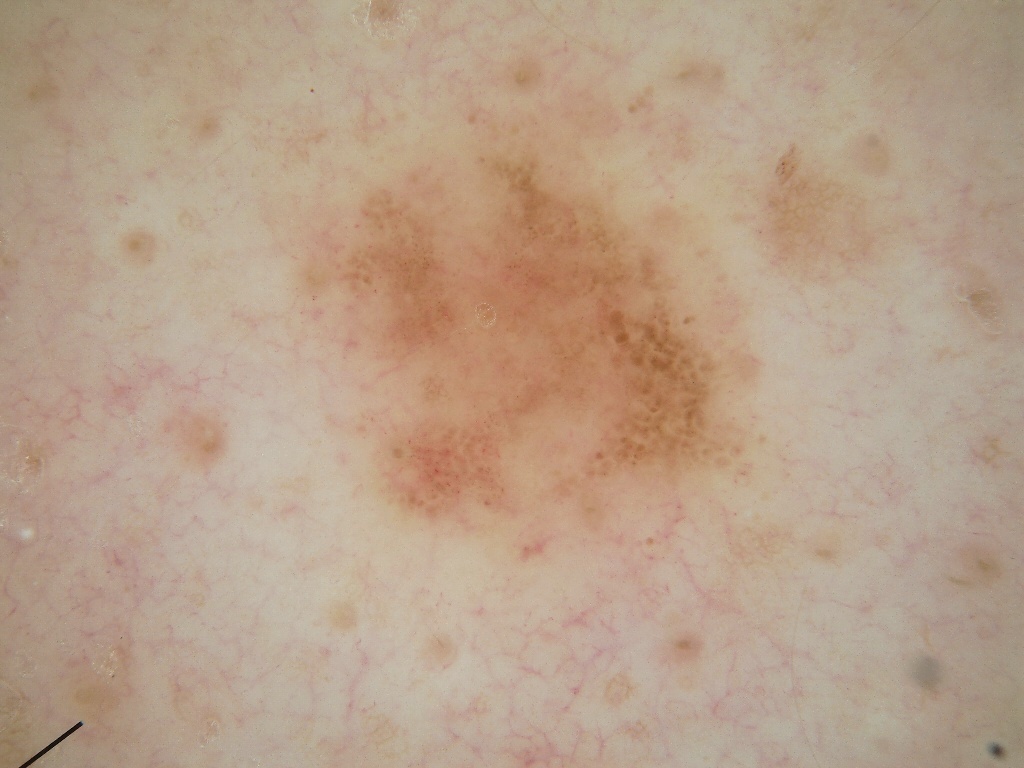- subject — male, aged 33-37
- imaging — dermoscopy of a skin lesion
- location — [246, 92, 771, 585]
- dermoscopic features — negative network, pigment network, and globules; absent: milia-like cysts and streaks
- diagnosis — a melanocytic nevus